Reported lesion symptoms include itching, no constitutional symptoms were reported, the photograph was taken at an angle, the lesion involves the leg and top or side of the foot, the condition has been present for about one day, the patient considered this acne, texture is reported as raised or bumpy — 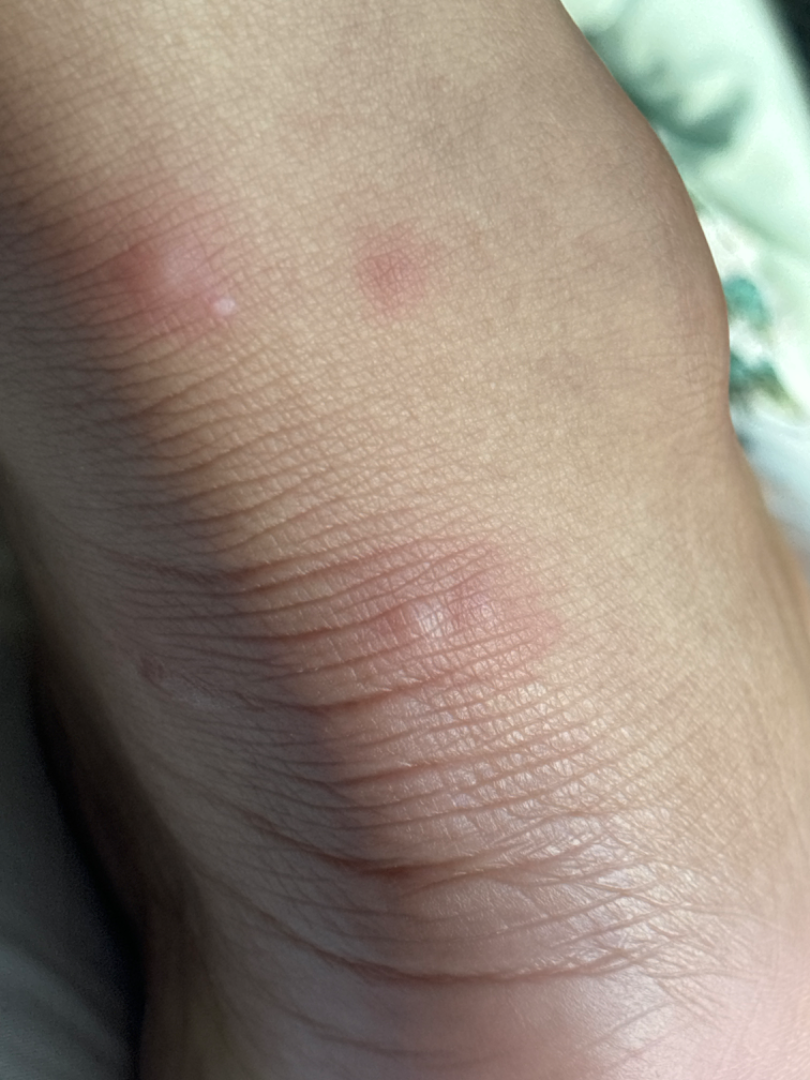{"differential": {"leading": ["Insect Bite"]}}